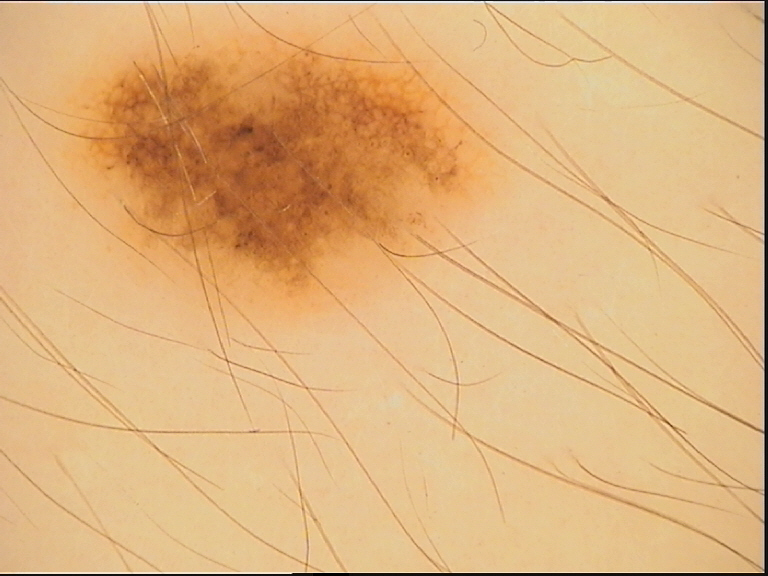imaging: dermatoscopy
diagnosis: dysplastic compound nevus (expert consensus)